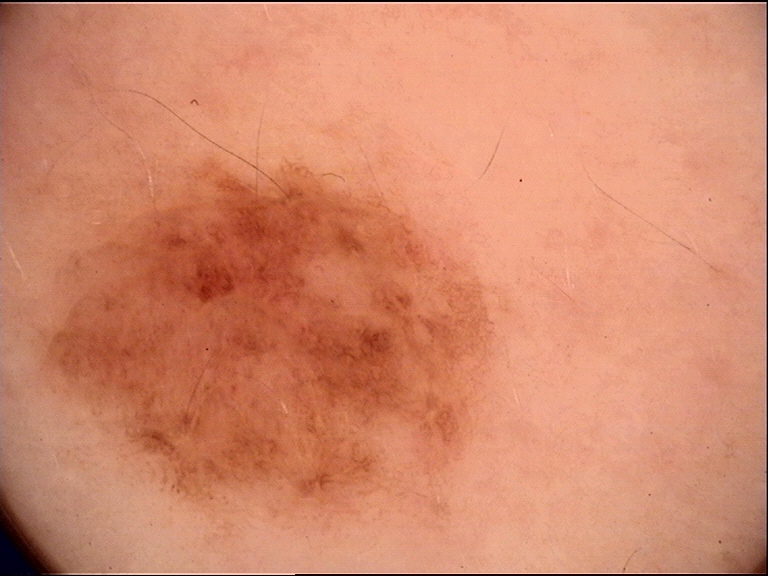image type — dermatoscopy
lesion type — banal
assessment — compound nevus (expert consensus)